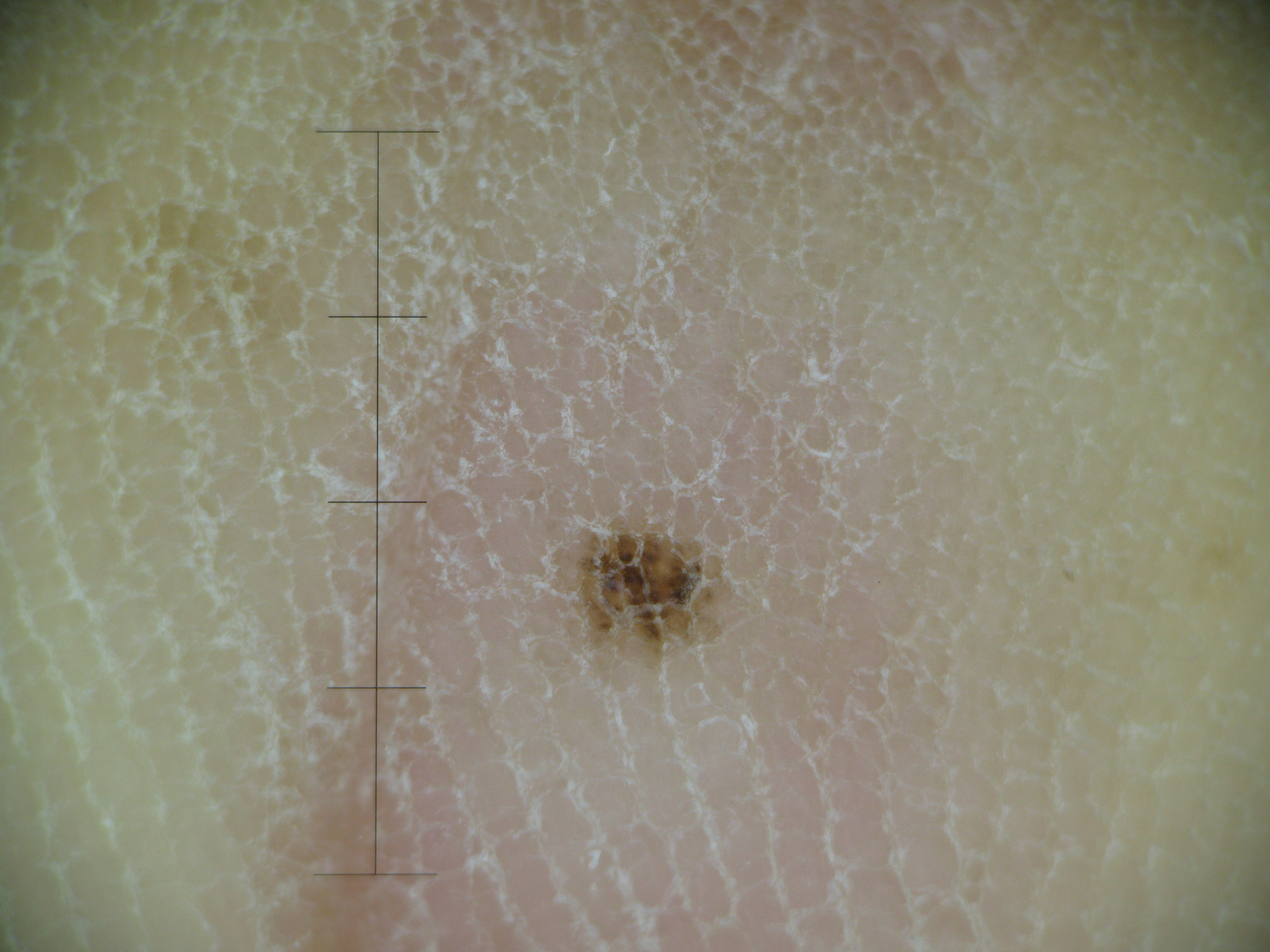image=dermatoscopy | assessment=acral dysplastic junctional nevus (expert consensus).